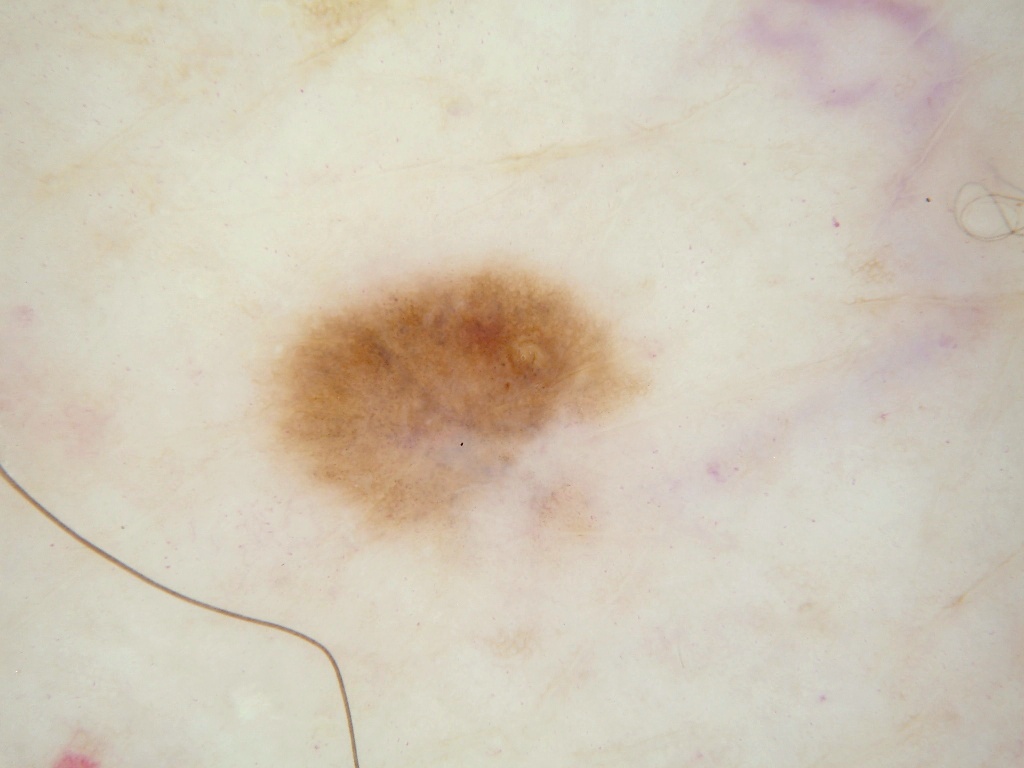<record>
<image>
  <modality>dermoscopy</modality>
</image>
<patient>
  <sex>female</sex>
  <age_approx>65</age_approx>
</patient>
<dermoscopic_features>
  <present>globules</present>
  <absent>milia-like cysts, streaks, negative network, pigment network</absent>
</dermoscopic_features>
<lesion_location>
  <bbox_xyxy>234, 246, 662, 585</bbox_xyxy>
</lesion_location>
<diagnosis>
  <name>melanocytic nevus</name>
  <malignancy>benign</malignancy>
  <lineage>melanocytic</lineage>
  <provenance>clinical</provenance>
</diagnosis>
</record>